The patient says their skin reddens with sun exposure. A female patient age 53. Dermoscopy of a skin lesion. Collected as part of a research study, without a referral diagnosis: 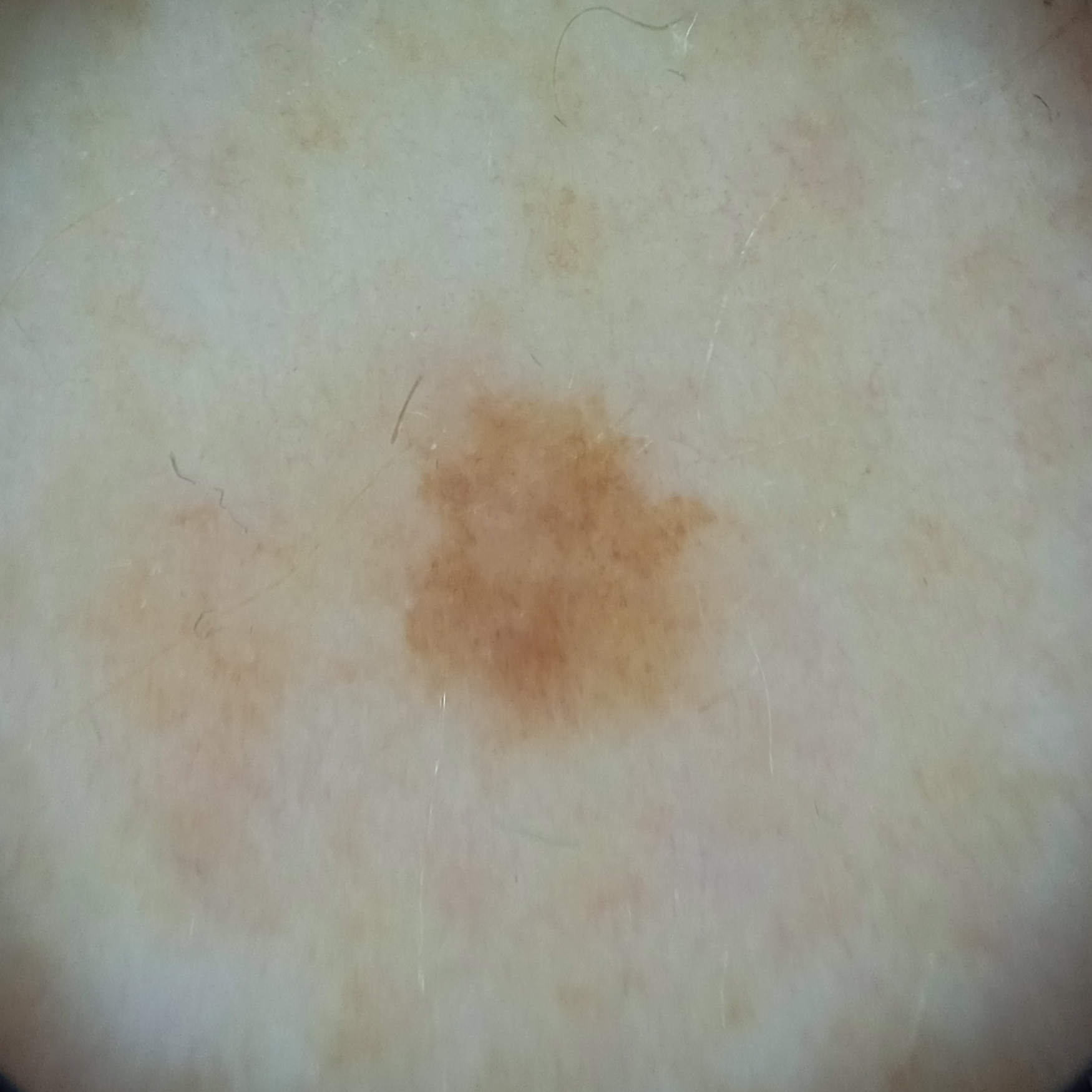The lesion is on a leg.
The lesion is about 4.1 mm across.
Dermatologist review favored a melanocytic nevus.